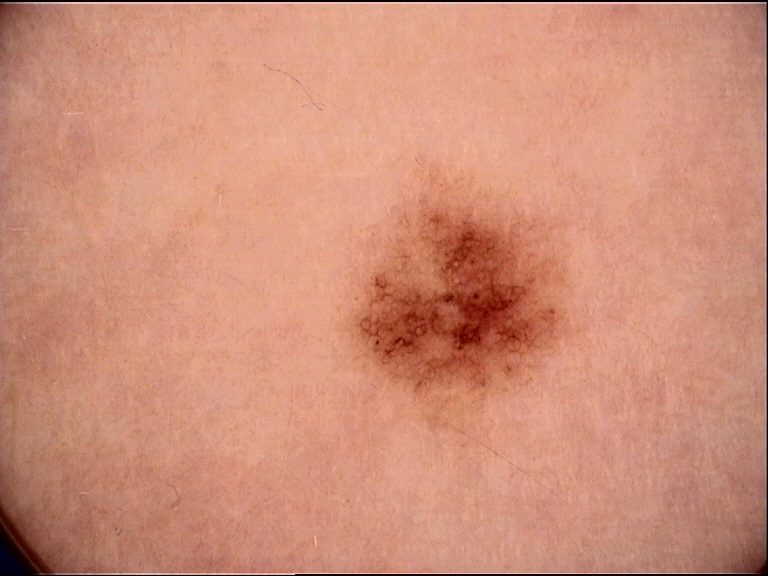Conclusion: The diagnostic label was a dysplastic junctional nevus.